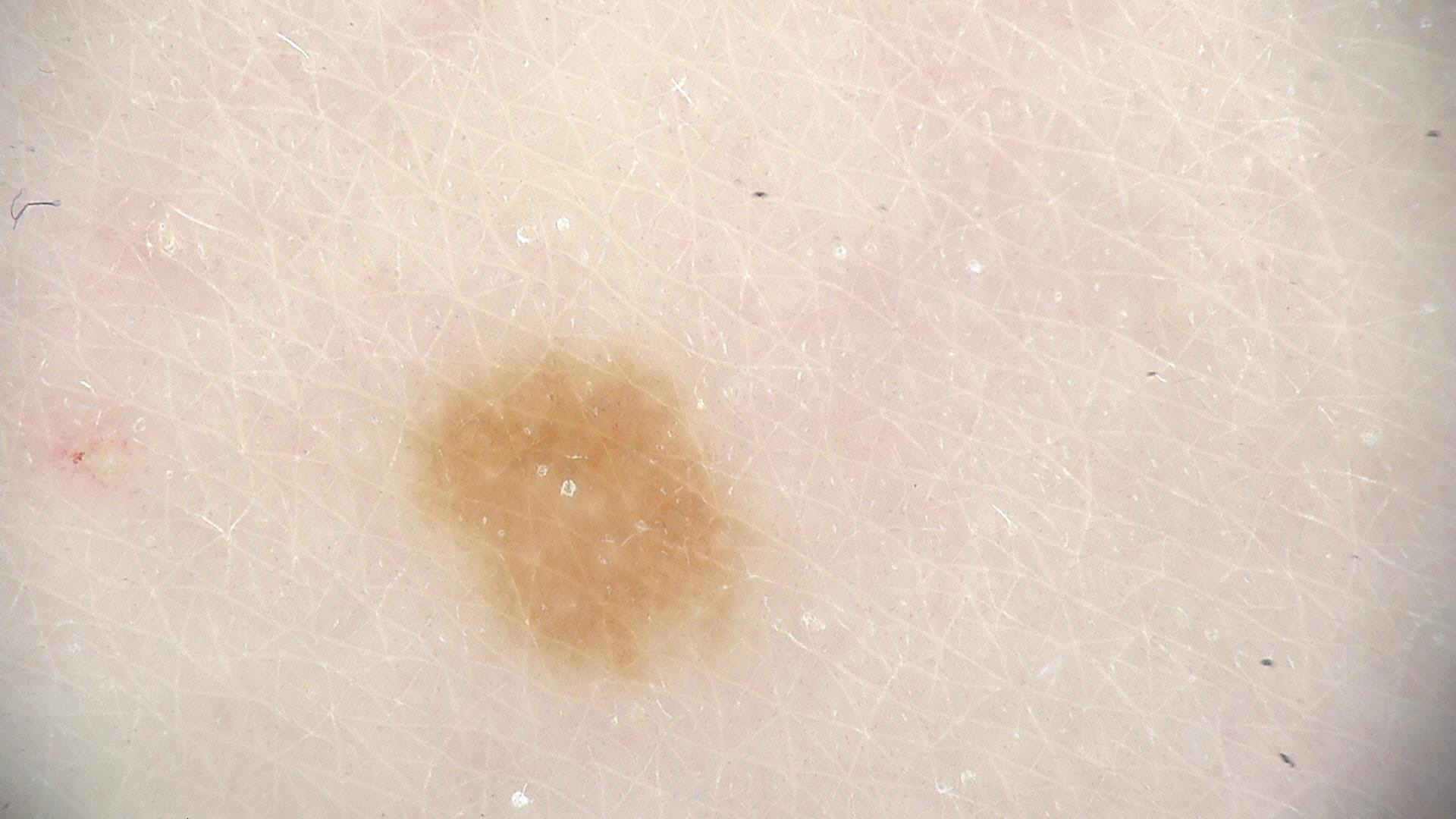| field | value |
|---|---|
| modality | dermoscopy |
| label | junctional nevus (expert consensus) |